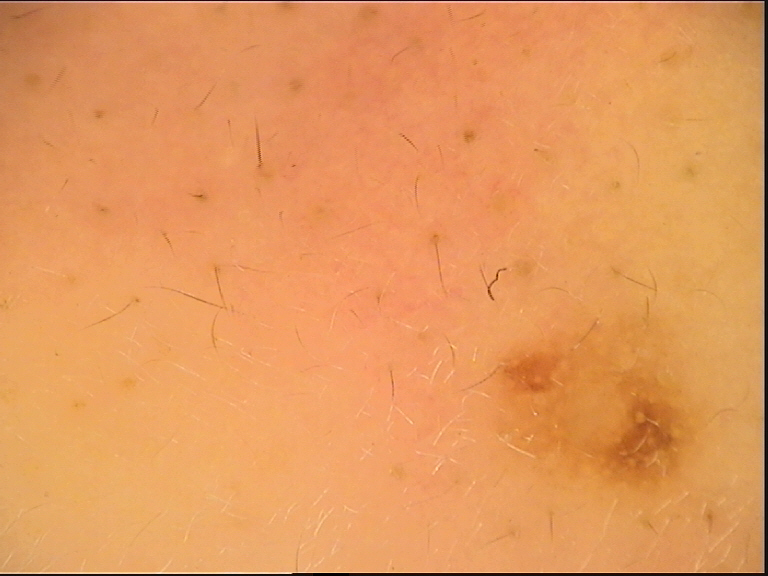Summary: A dermoscopy image of a single skin lesion. Impression: Diagnosed as a compound nevus.